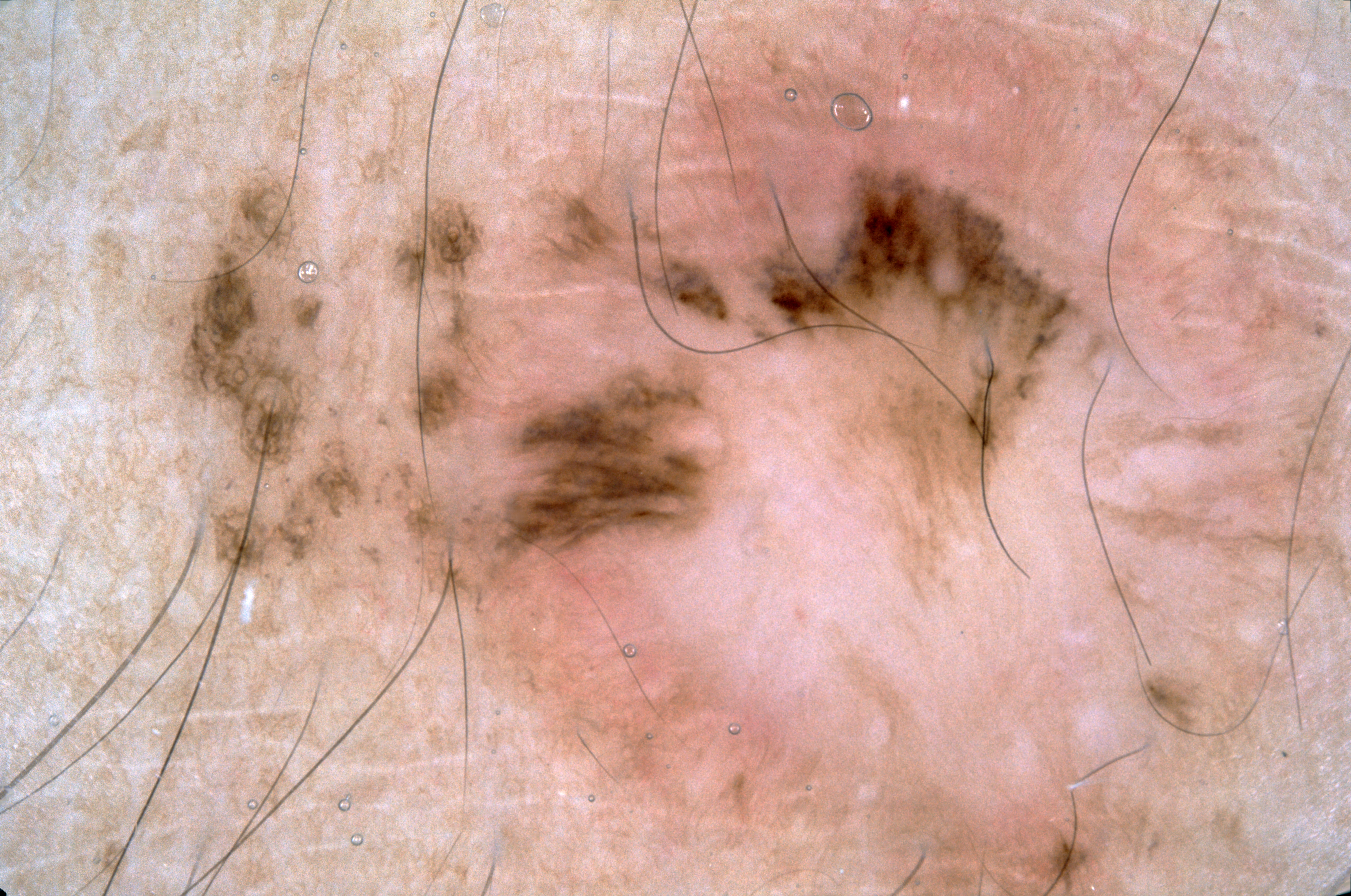Case summary: Dermoscopy of a skin lesion. Dermoscopy demonstrates pigment network; no streaks, negative network, or milia-like cysts. The lesion is located at left=154, top=5, right=1345, bottom=892. Impression: Expert review diagnosed this as a melanocytic nevus, a benign lesion.